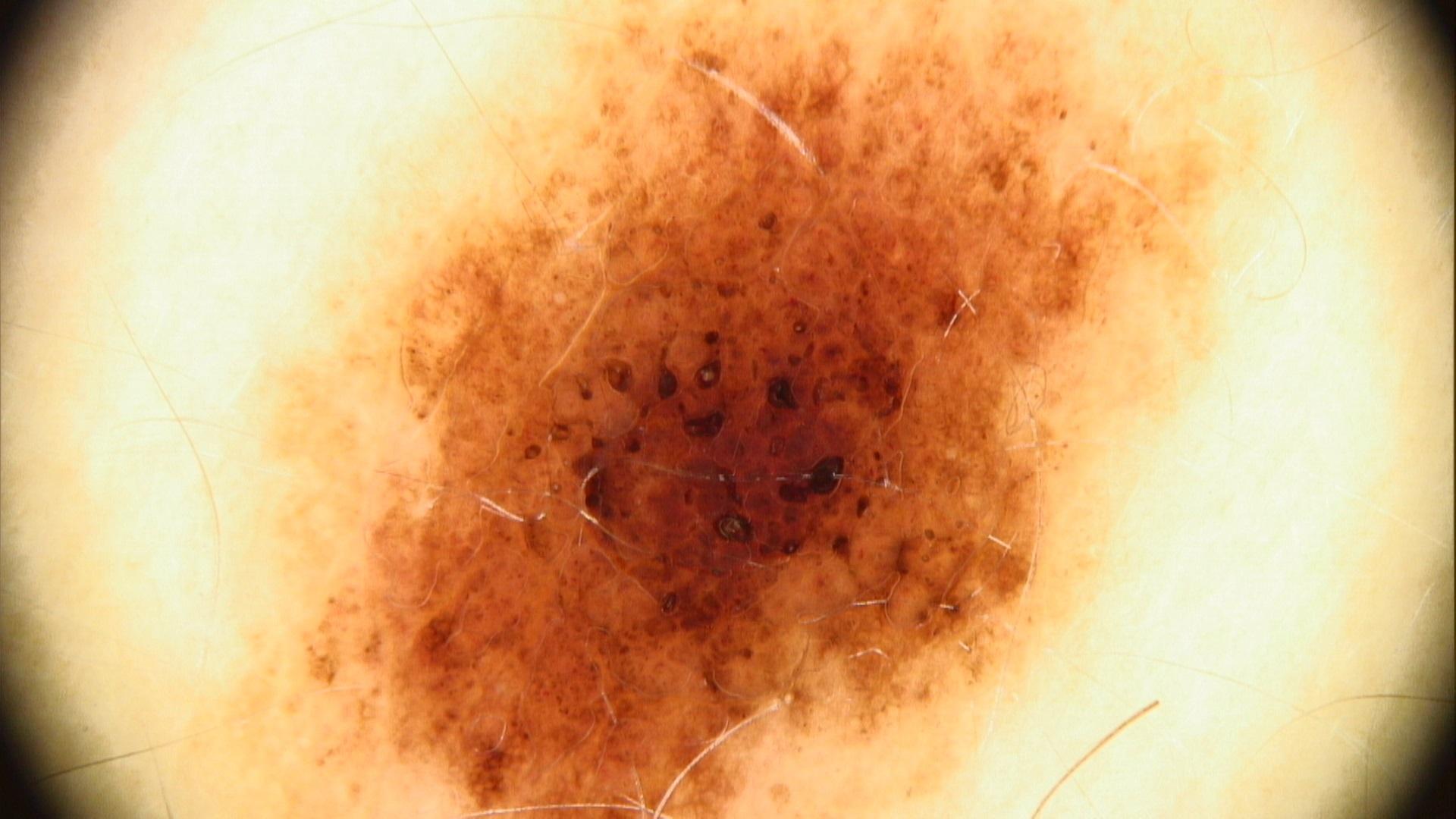A female subject aged around 30. Dermoscopy of a skin lesion. The lesion is on the trunk. Clinically diagnosed as a nevus.